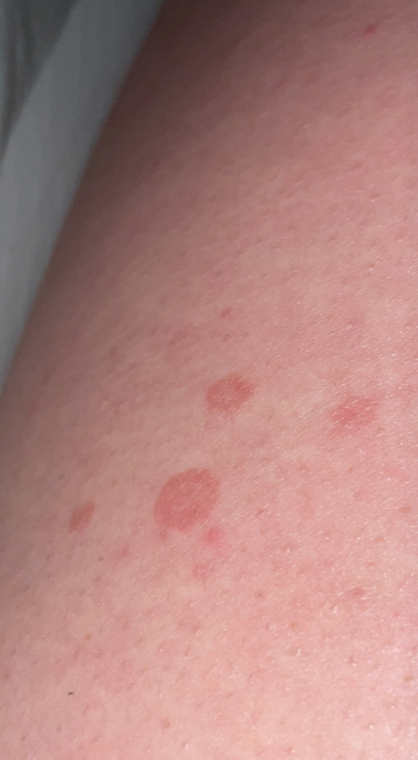assessment — indeterminate | skin tone — Fitzpatrick skin type II | affected area — back of the torso | associated systemic symptoms — none reported | framing — close-up | patient's own categorization — skin that appeared healthy to them | present for — about one day | described texture — flat.